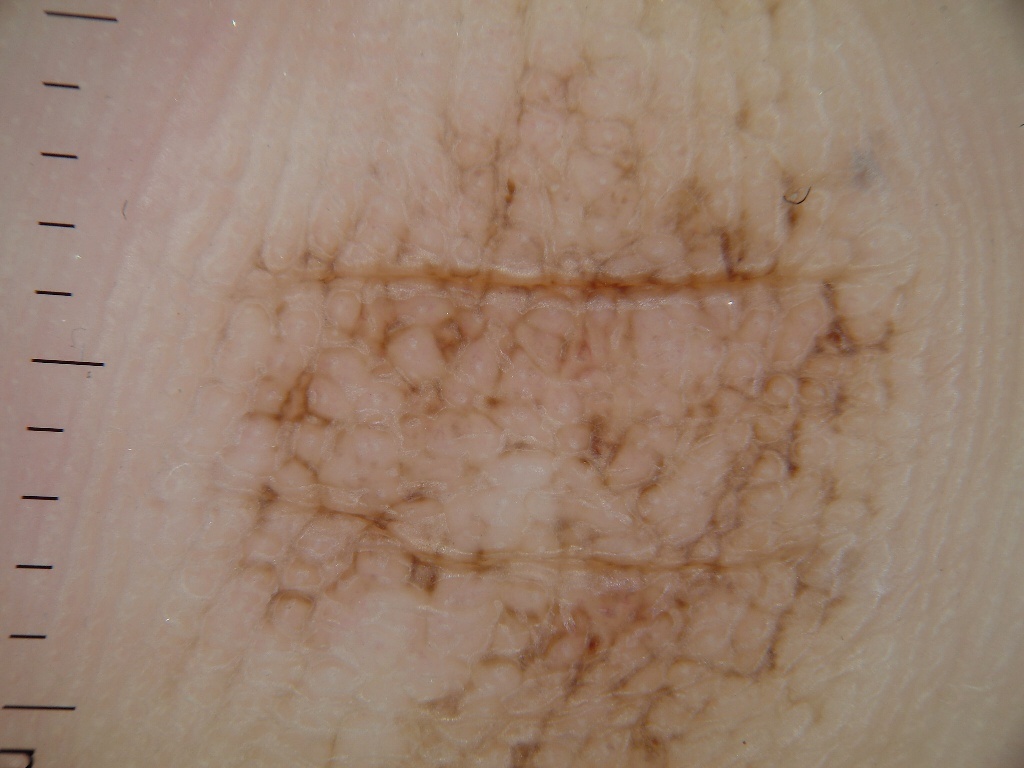Findings:
- image · dermatoscopic image of a skin lesion
- absent dermoscopic findings · milia-like cysts, negative network, pigment network, globules, and streaks
- lesion extent · ~62% of the field
- lesion bbox · x1=174 y1=4 x2=944 y2=766
- assessment · a melanocytic nevus